A male patient roughly 75 years of age · a dermoscopy image of a single skin lesion.
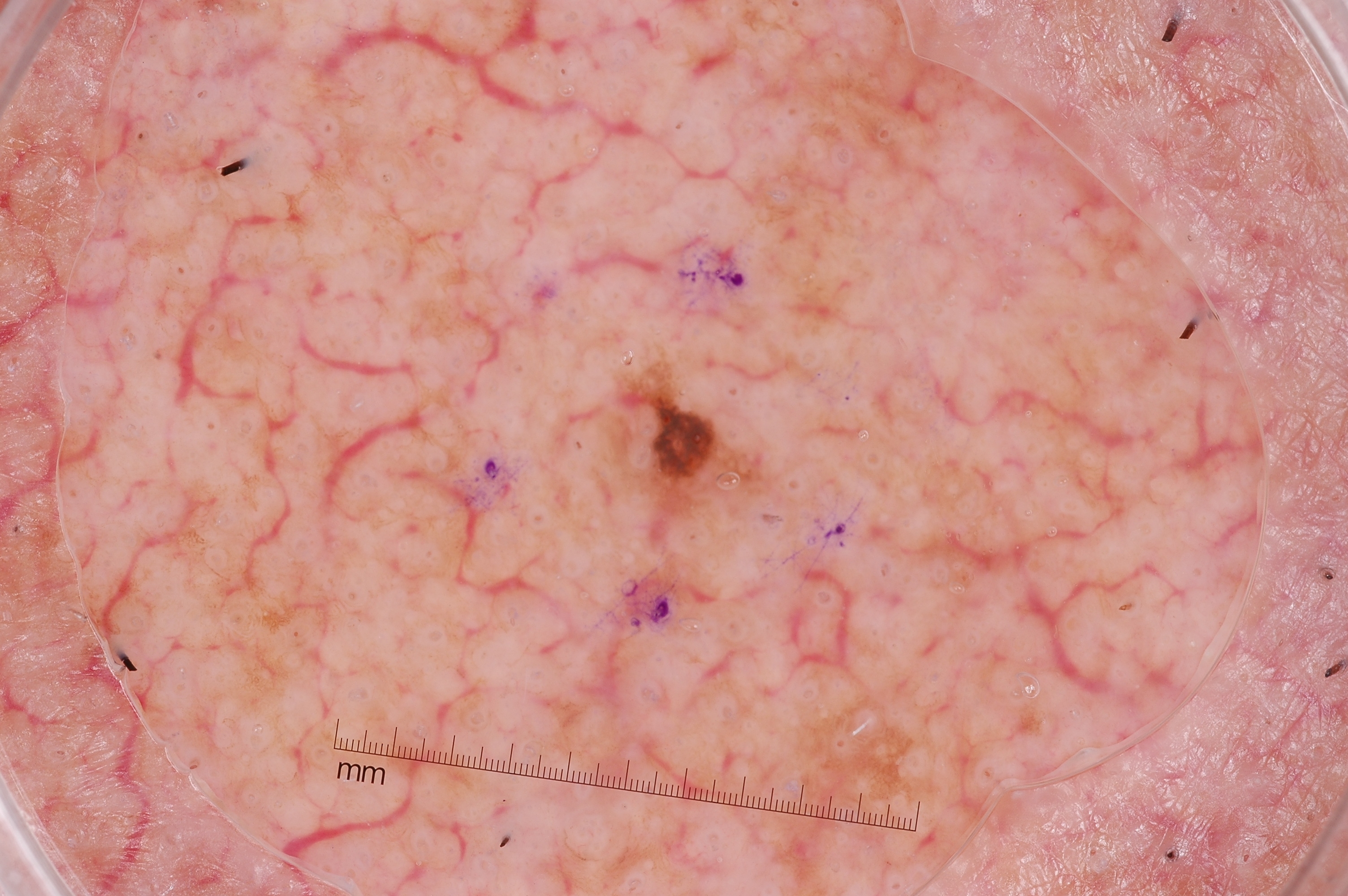{"dermoscopic_features": {"present": [], "absent": ["streaks", "negative network", "milia-like cysts", "pigment network"]}, "lesion_location": {"bbox_xyxy": [554, 352, 780, 551]}, "lesion_extent": "small", "diagnosis": {"name": "seborrheic keratosis", "malignancy": "benign", "lineage": "keratinocytic", "provenance": "clinical"}}